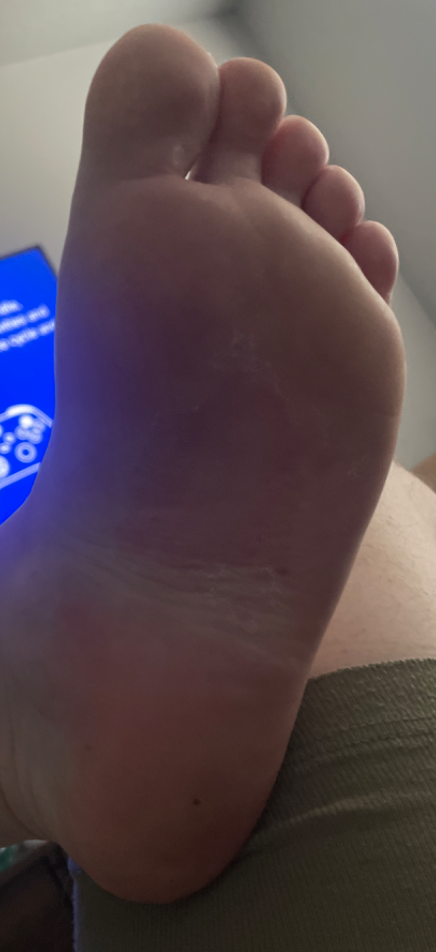assessment = ungradable on photographic review
patient = male, age 18–29
anatomic site = sole of the foot
duration = one to four weeks
symptoms = itching
view = at a distance
described texture = rough or flaky